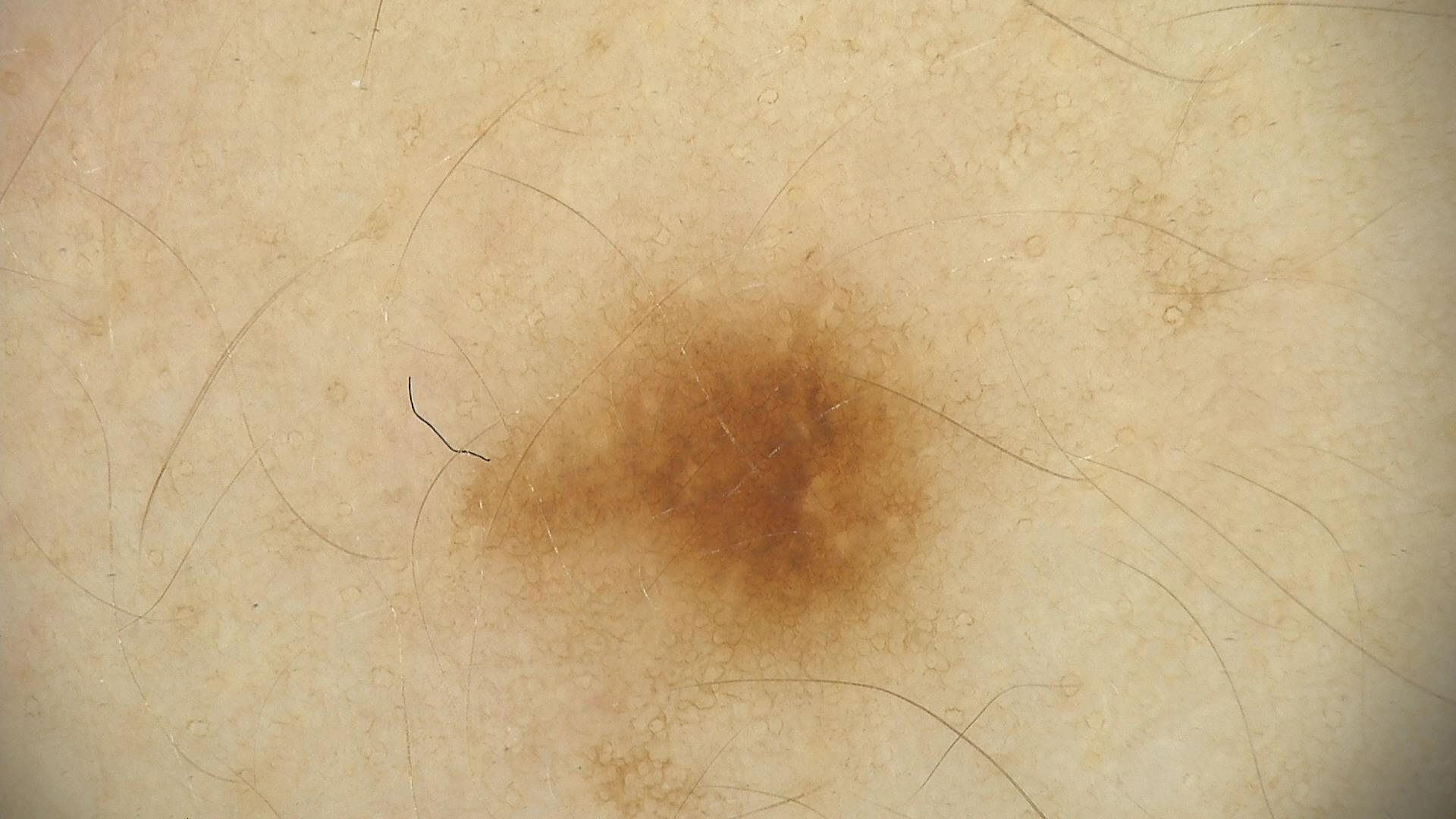Findings:
- diagnosis — dysplastic junctional nevus (expert consensus)